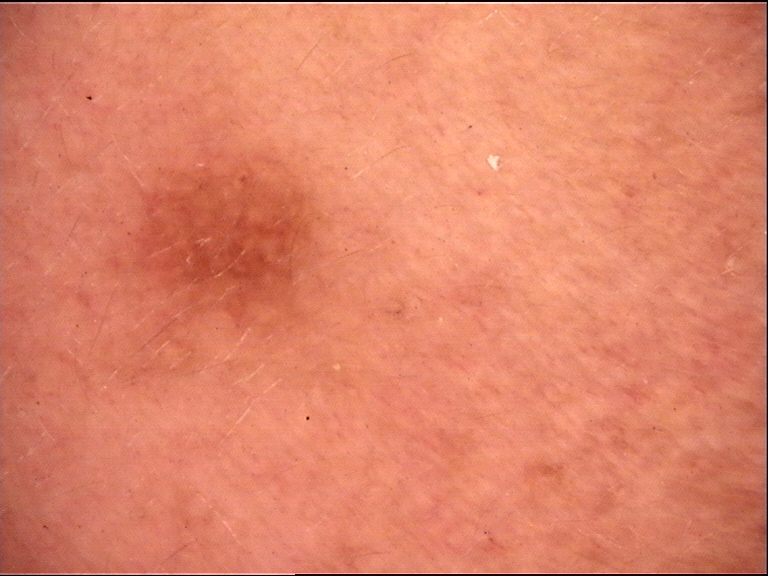The diagnostic label was a Miescher nevus.